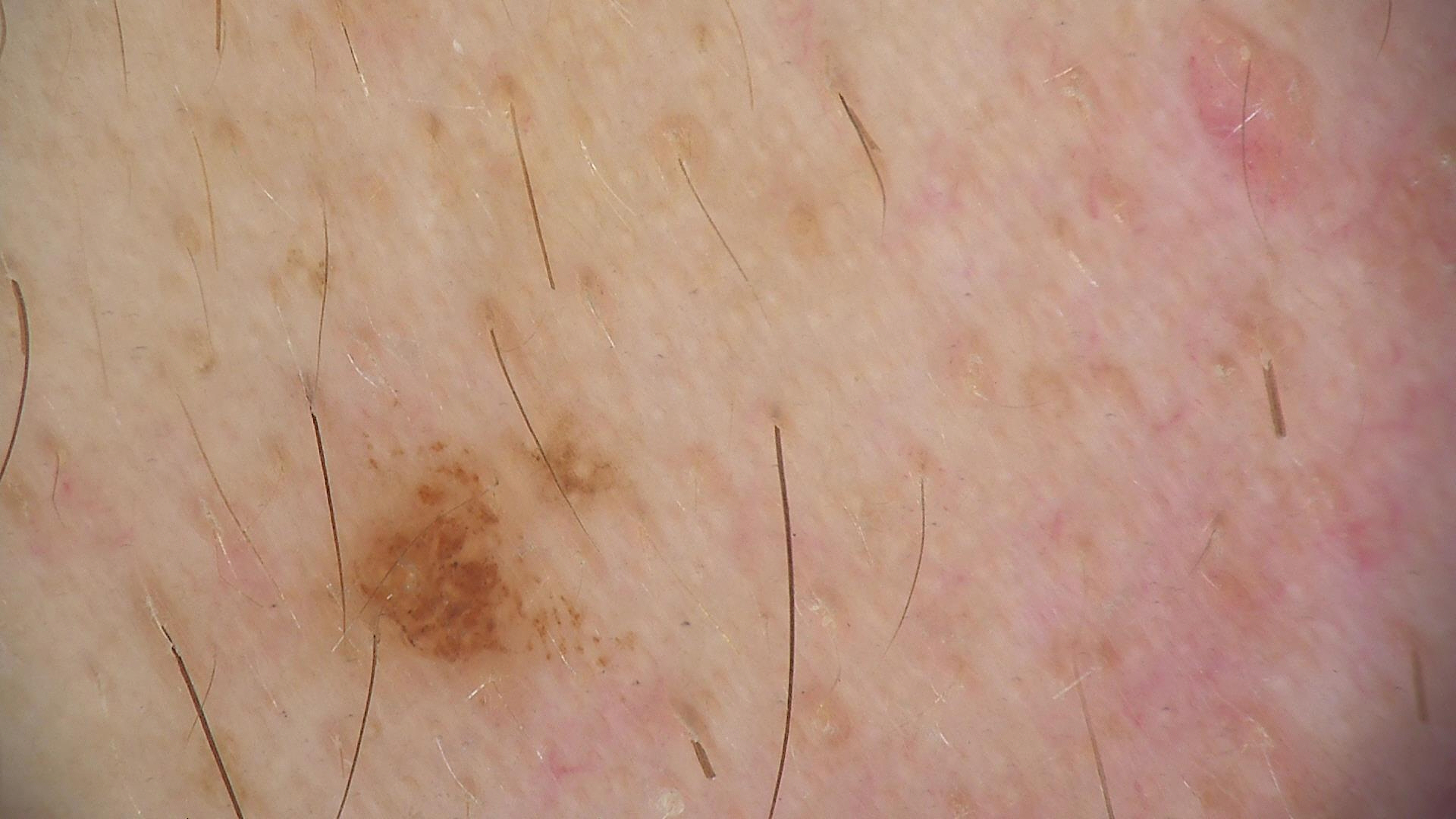Consistent with a dysplastic junctional nevus.